A dermoscopic close-up of a skin lesion:
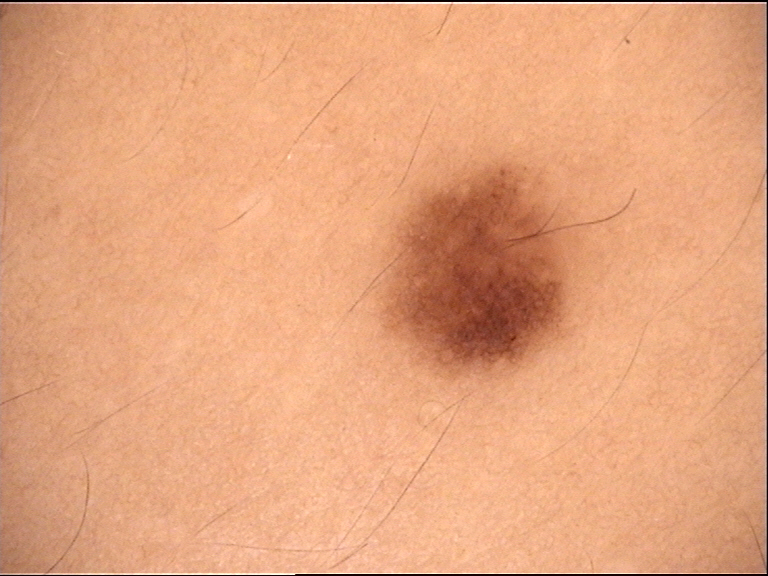diagnostic label = compound nevus (expert consensus)